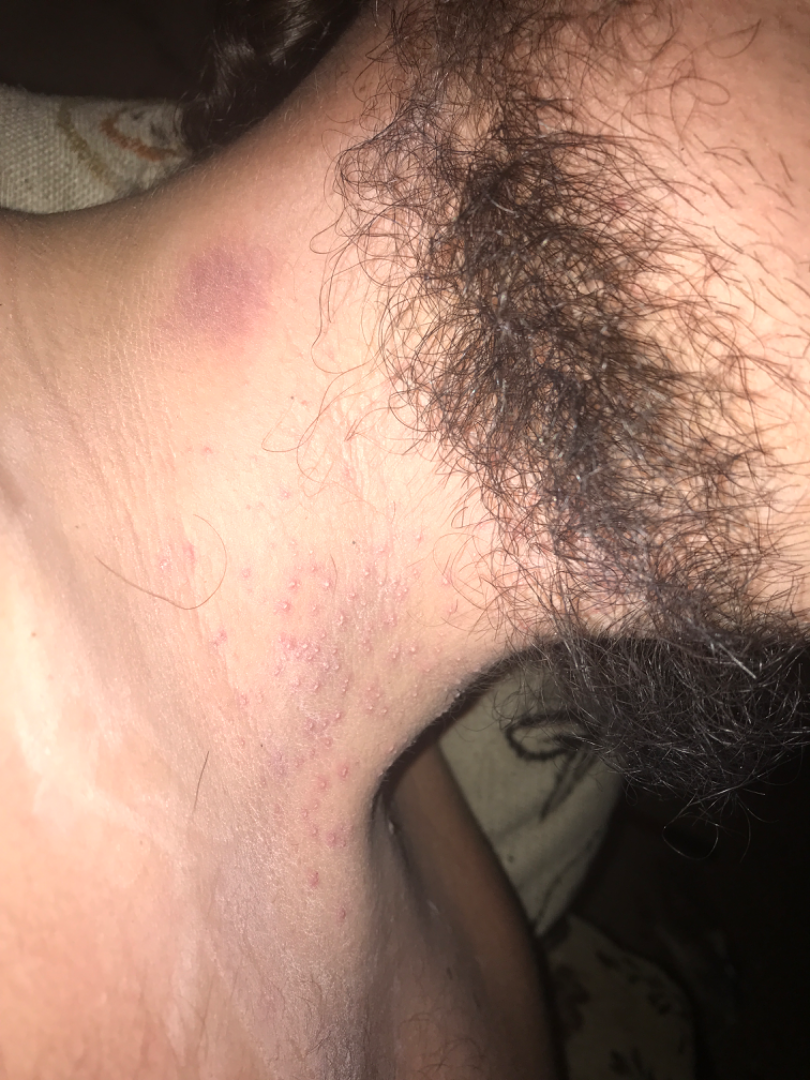Texture is reported as raised or bumpy. The photo was captured at an angle. On photographic review: Folliculitis (weight 1.00).